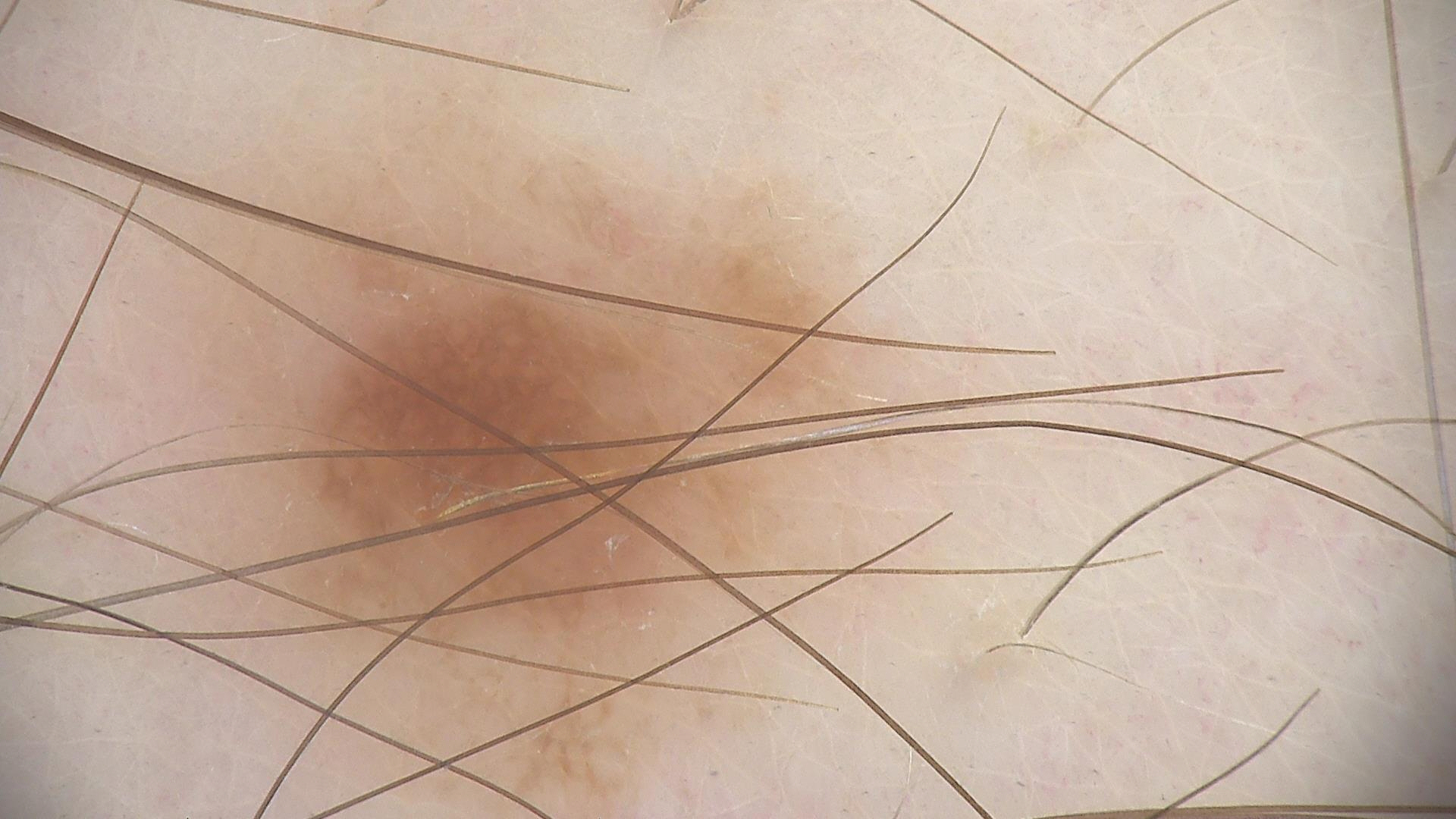image: dermoscopy, label: dysplastic junctional nevus (expert consensus).